The contributor reports the lesion is raised or bumpy · reported lesion symptoms include burning · self-categorized by the patient as a rash · the affected area is the arm · the contributor reports the condition has been present for about one day · the photograph was taken at a distance:
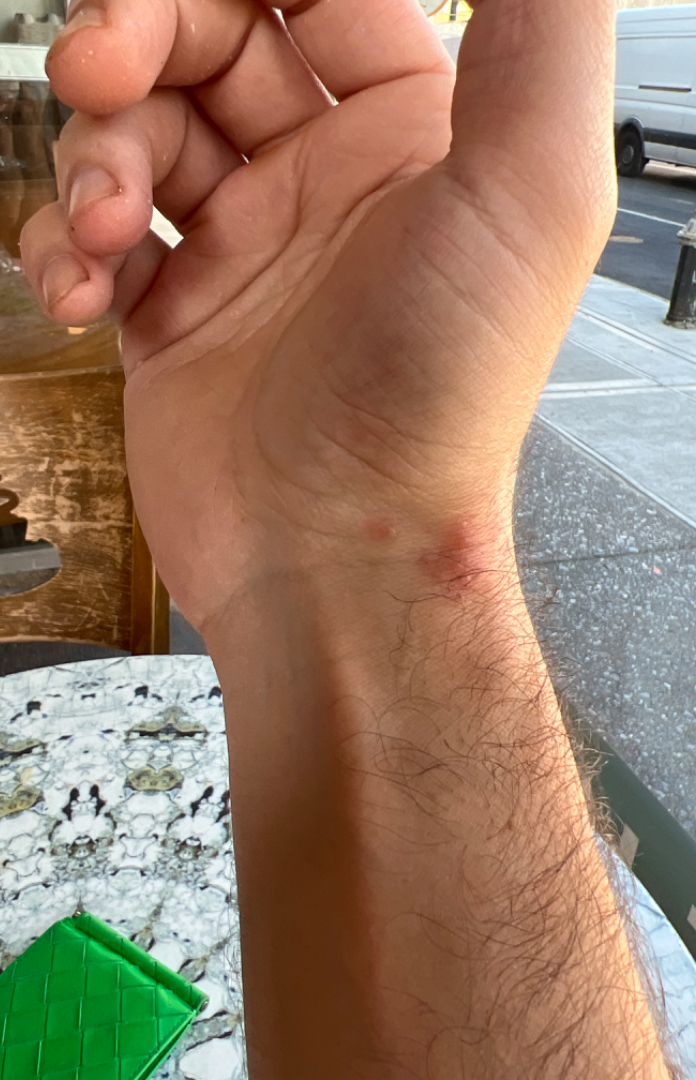<summary>
<differential>
  <leading>Insect Bite</leading>
  <considered>Eczema</considered>
  <unlikely>Allergic Contact Dermatitis</unlikely>
</differential>
</summary>